Female subject, age 18–29 · this image was taken at a distance · the arm, front of the torso, leg and back of the torso are involved — 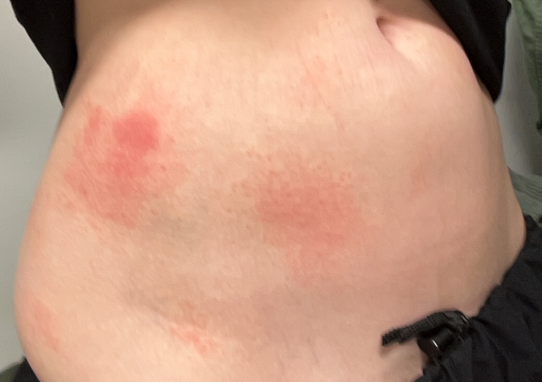dermatologist impression = three dermatologists independently reviewed the case: favoring Allergic Contact Dermatitis; the differential also includes Sweet syndrome.